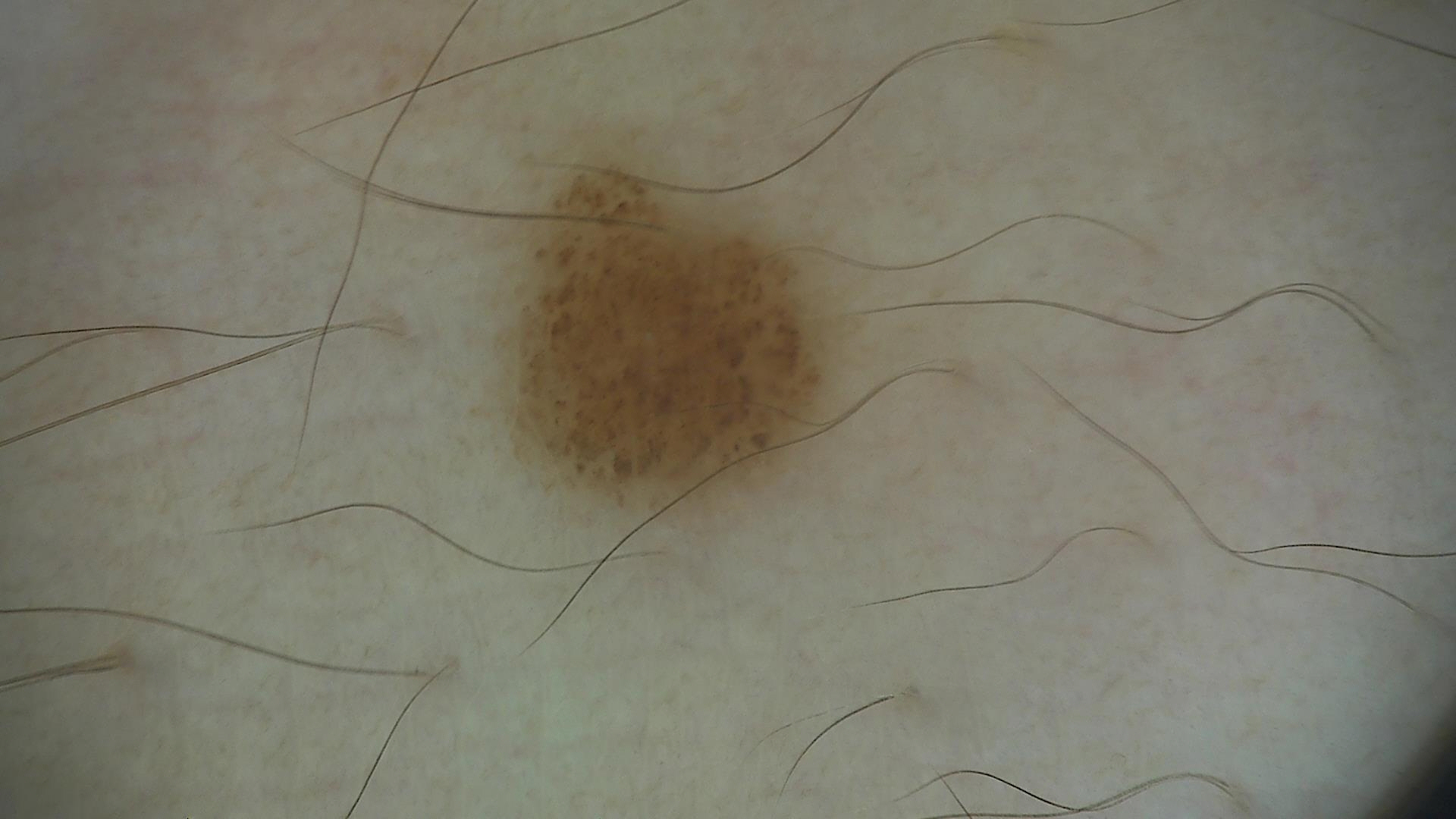The diagnosis was a dysplastic junctional nevus.